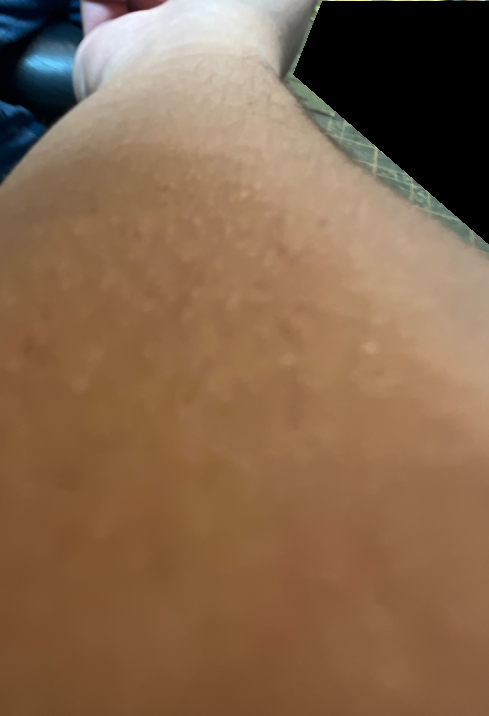shot_type: at an angle
body_site:
  - head or neck
  - arm
texture:
  - raised or bumpy
  - flat
symptoms: burning
patient_category: a rash
differential:
  leading:
    - Eczema
  considered:
    - Allergic Contact Dermatitis